The patient is Fitzpatrick skin type II · a smartphone photograph of a skin lesion · a male subject aged 61: 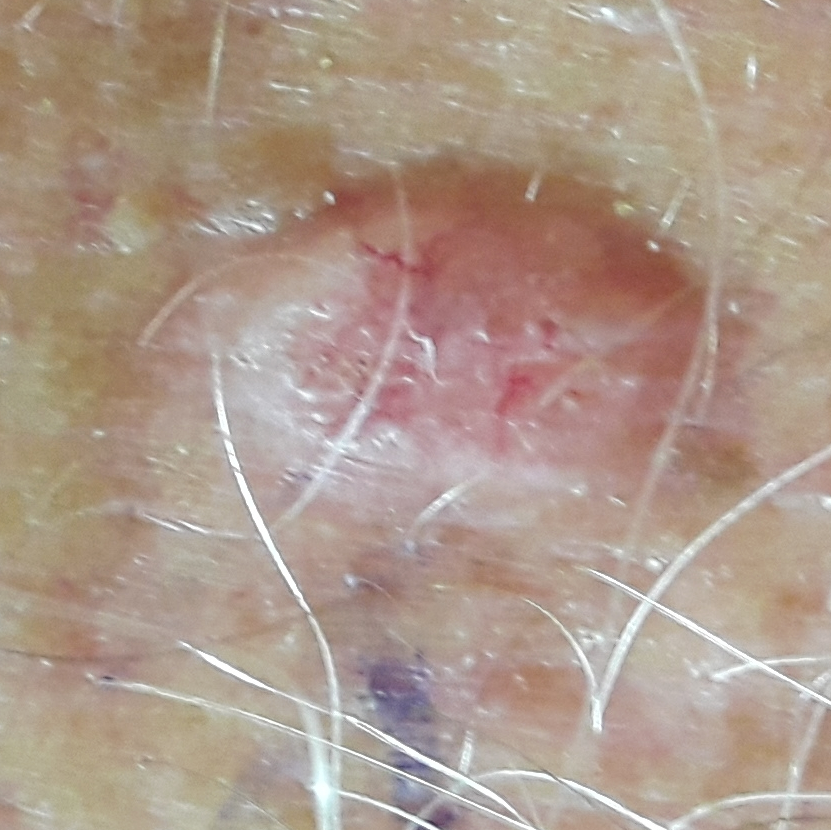Q: Where on the body is the lesion?
A: the chest
Q: What are the lesion's dimensions?
A: 9x7 mm
Q: What does the patient describe?
A: itching, elevation
Q: What is this lesion?
A: basal cell carcinoma (biopsy-proven)